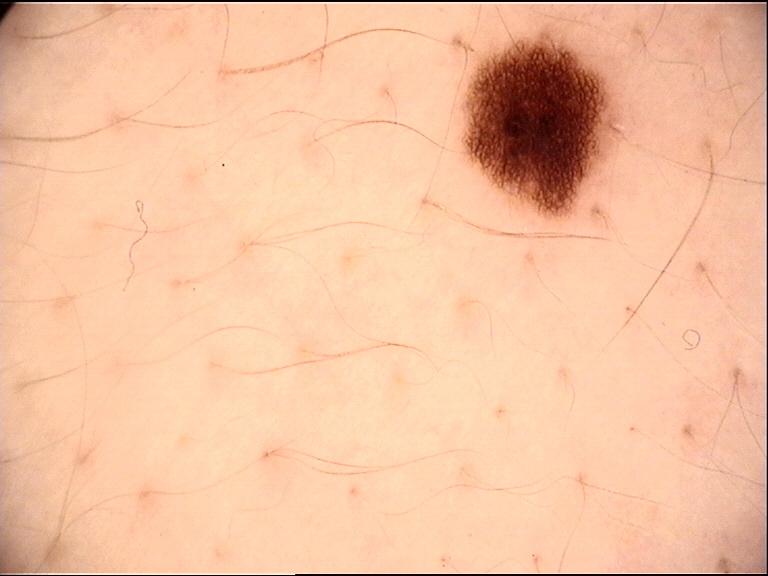A dermoscopic close-up of a skin lesion. Classified as a benign lesion — a dysplastic junctional nevus.